The chart notes a prior melanoma; FST II — 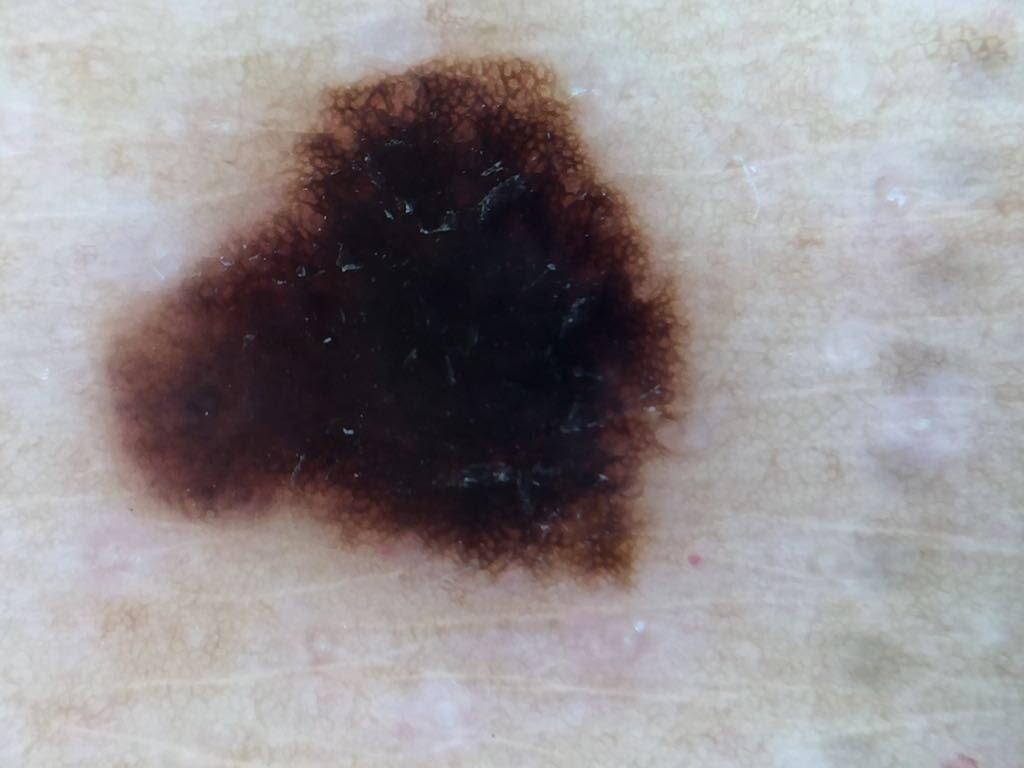Case summary:
The lesion is located on the posterior trunk.
Conclusion:
Biopsy-confirmed as a melanoma.